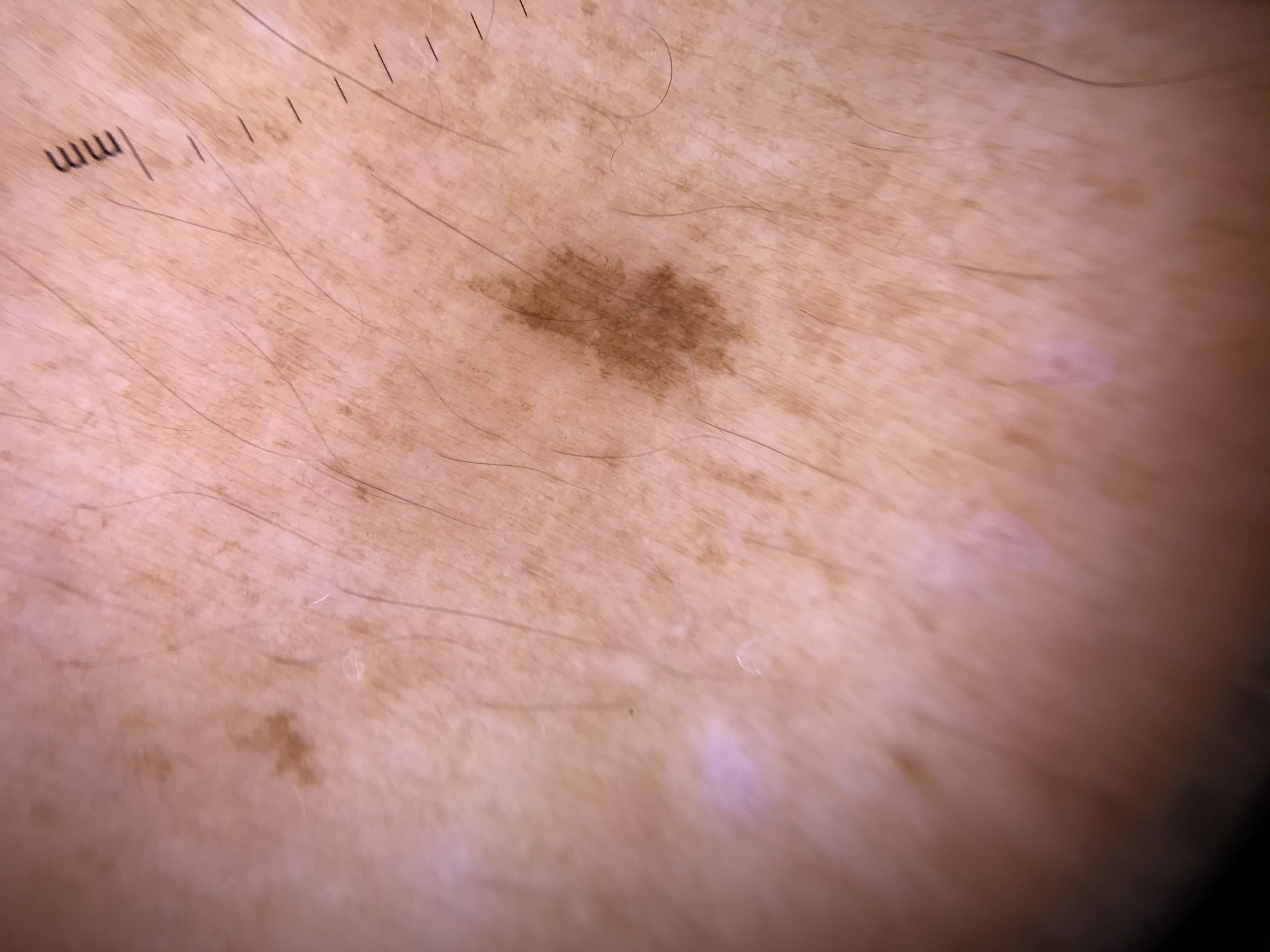Classified as a solar lentigo.